The patient is a female roughly 80 years of age, a dermoscopic close-up of a skin lesion:
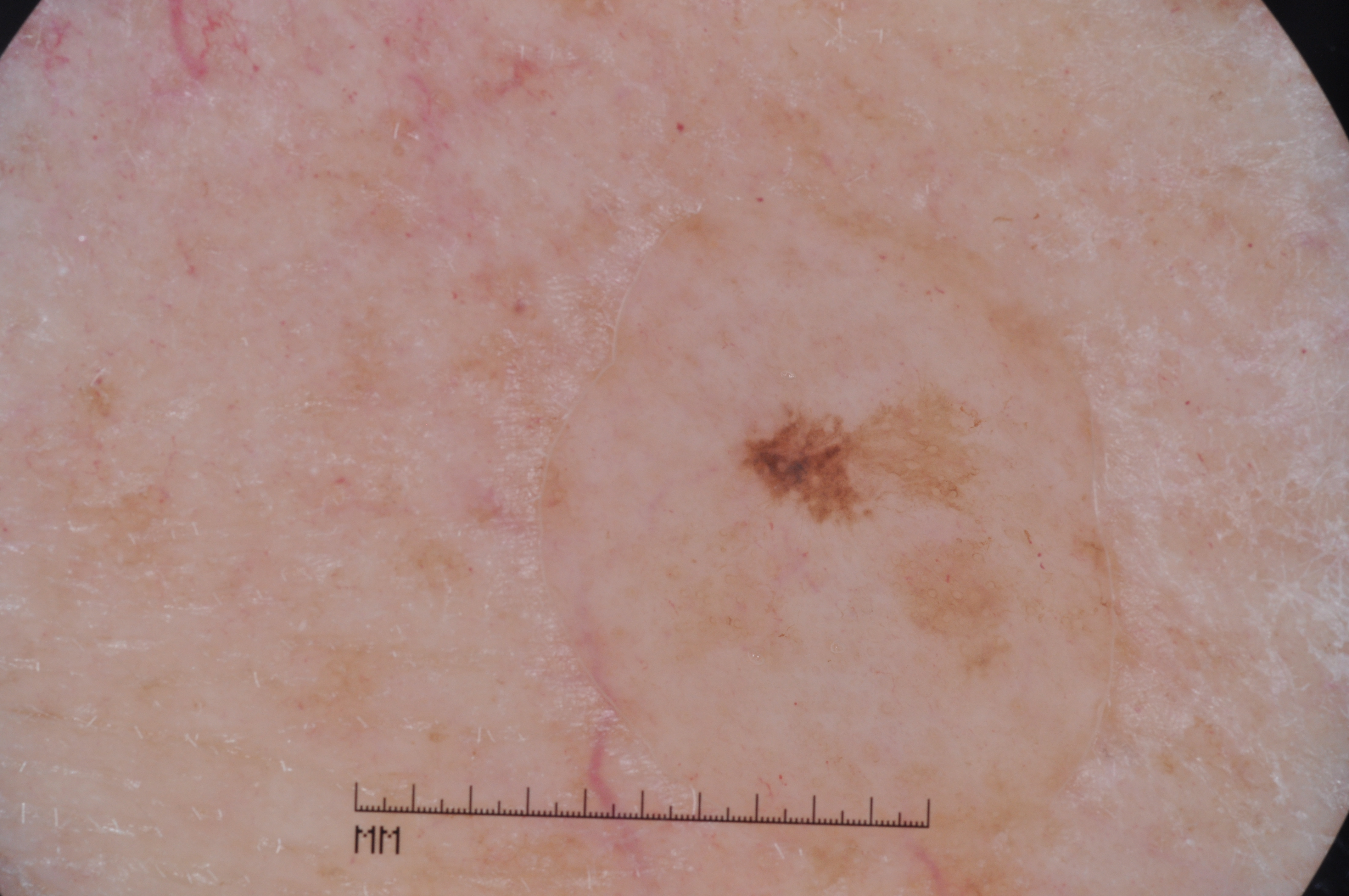location: 648/338/1067/719 | lesion extent: ~10% of the field | dermoscopic features assessed but absent: pigment network, negative network, milia-like cysts, and streaks | assessment: a melanoma, a malignant skin lesion.